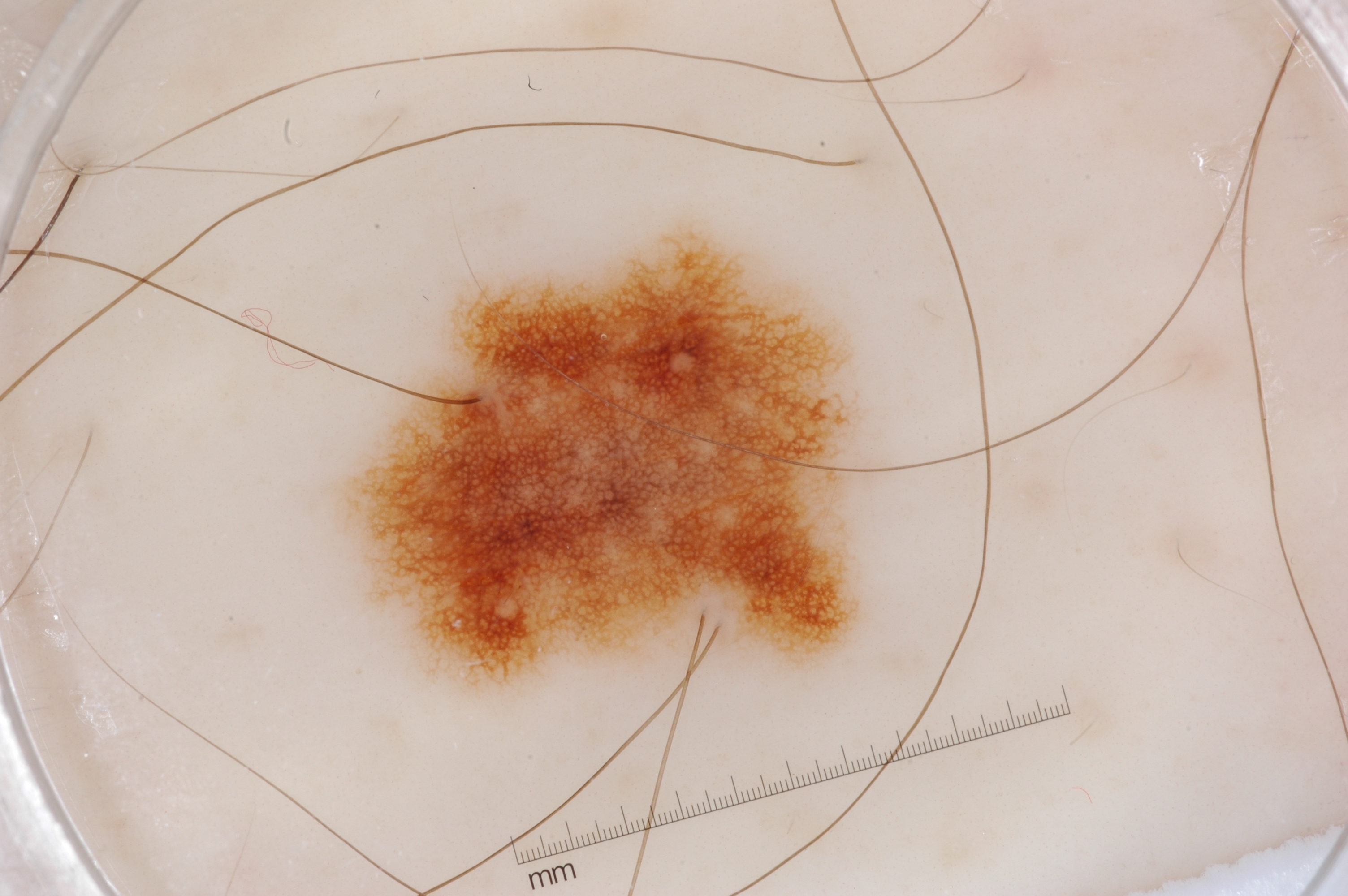  image:
    modality: dermoscopy
  lesion_location:
    bbox_xyxy:
      - 358
      - 238
      - 853
      - 679
  diagnosis:
    name: melanocytic nevus
    malignancy: benign
    lineage: melanocytic
    provenance: clinical